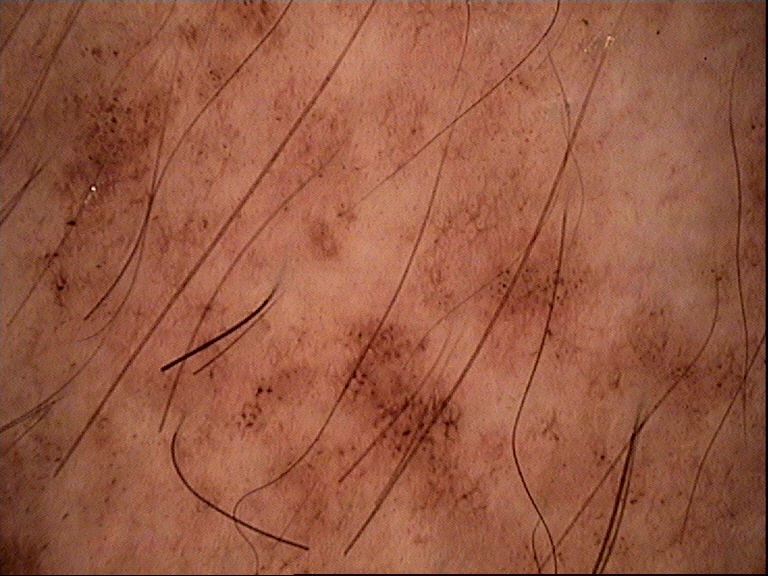Findings:
– assessment — congenital junctional nevus (expert consensus)